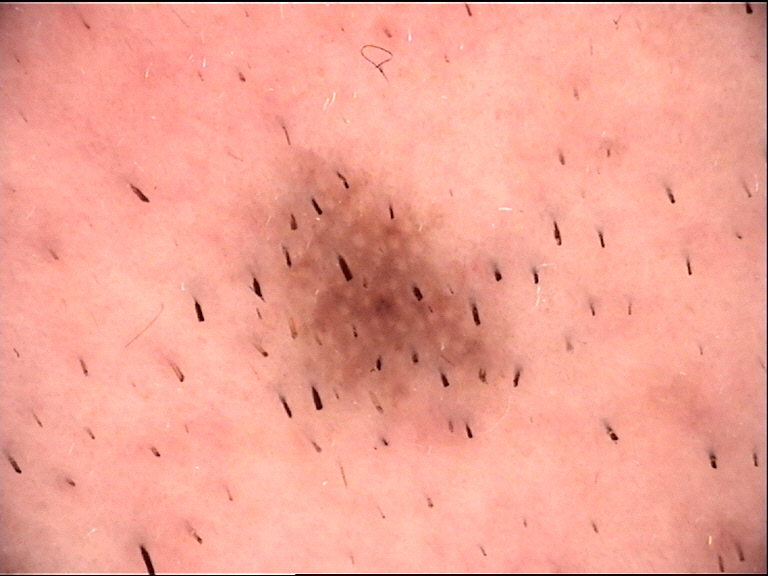A dermoscopic image of a skin lesion.
The architecture is that of a banal, compound lesion.
Labeled as a Miescher nevus.